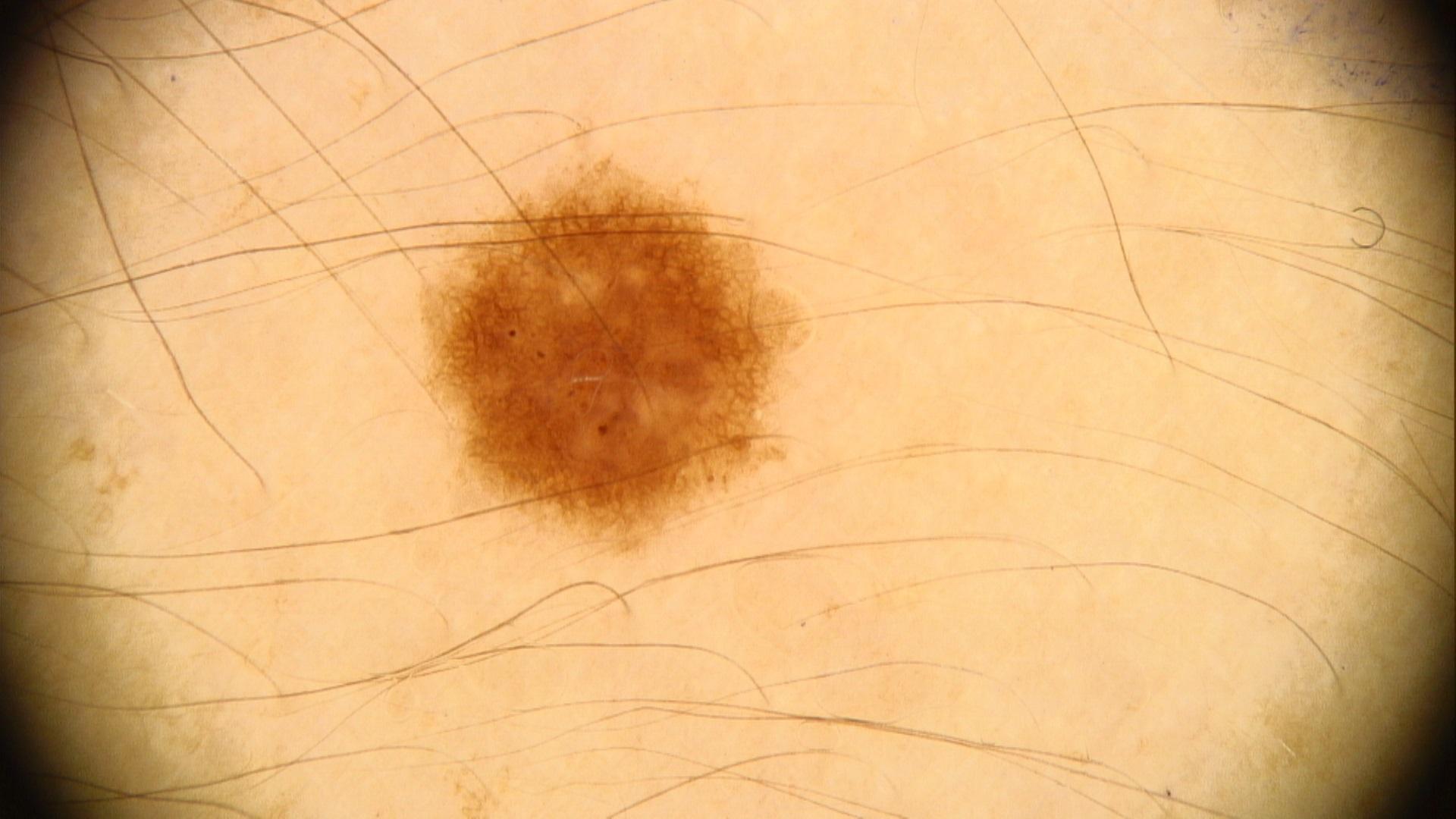{"image": "contact-polarized dermoscopy", "patient": {"age_approx": 20, "sex": "female"}, "melanoma_history": {"family_hx_melanoma": true}, "skin_type": "III", "lesion_location": {"region": "an upper extremity"}, "diagnosis": {"name": "Nevus", "malignancy": "benign", "confirmation": "expert clinical impression", "lineage": "melanocytic"}}